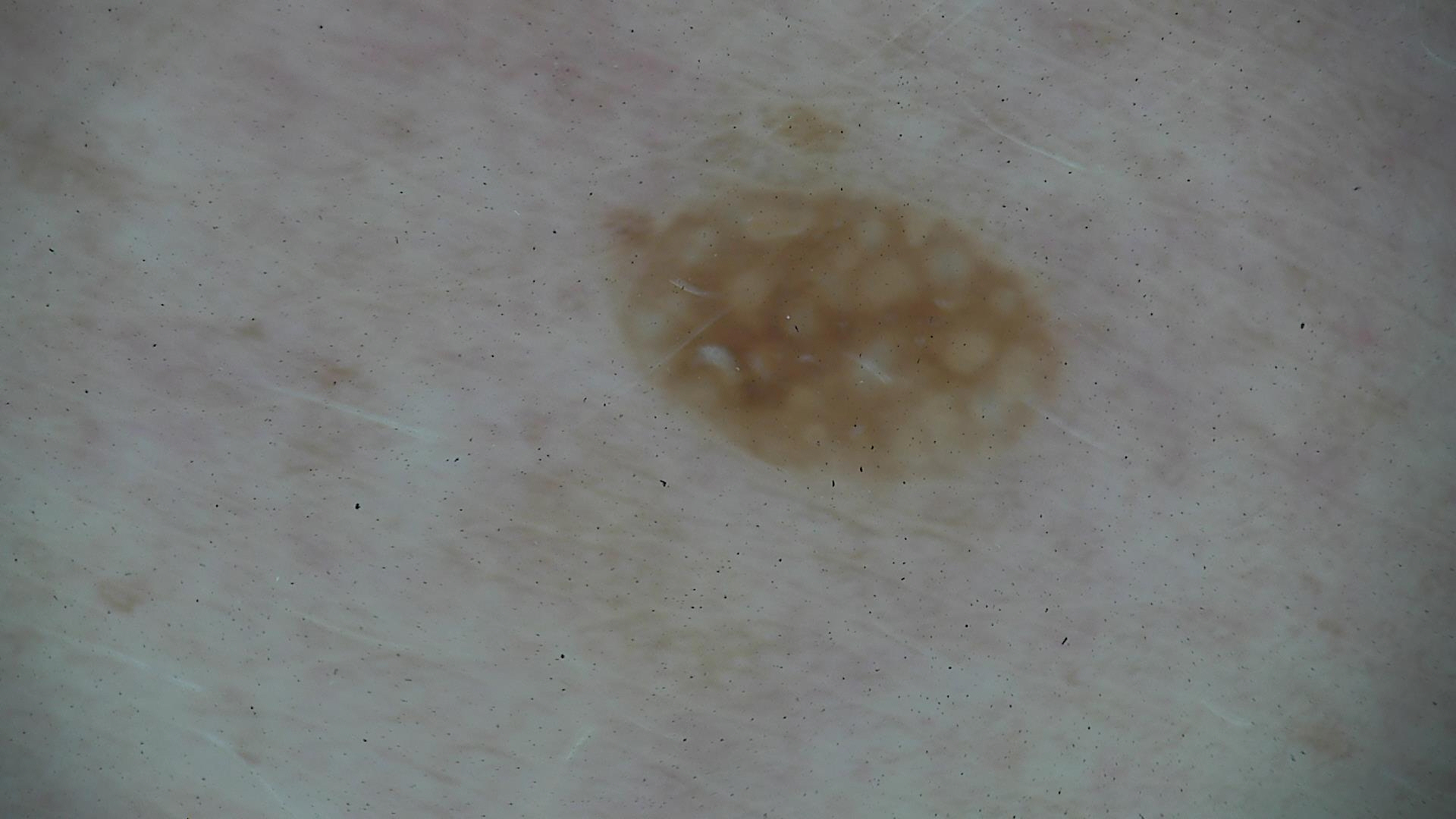| key | value |
|---|---|
| imaging | dermatoscopy |
| lesion type | keratinocytic |
| label | seborrheic keratosis (expert consensus) |